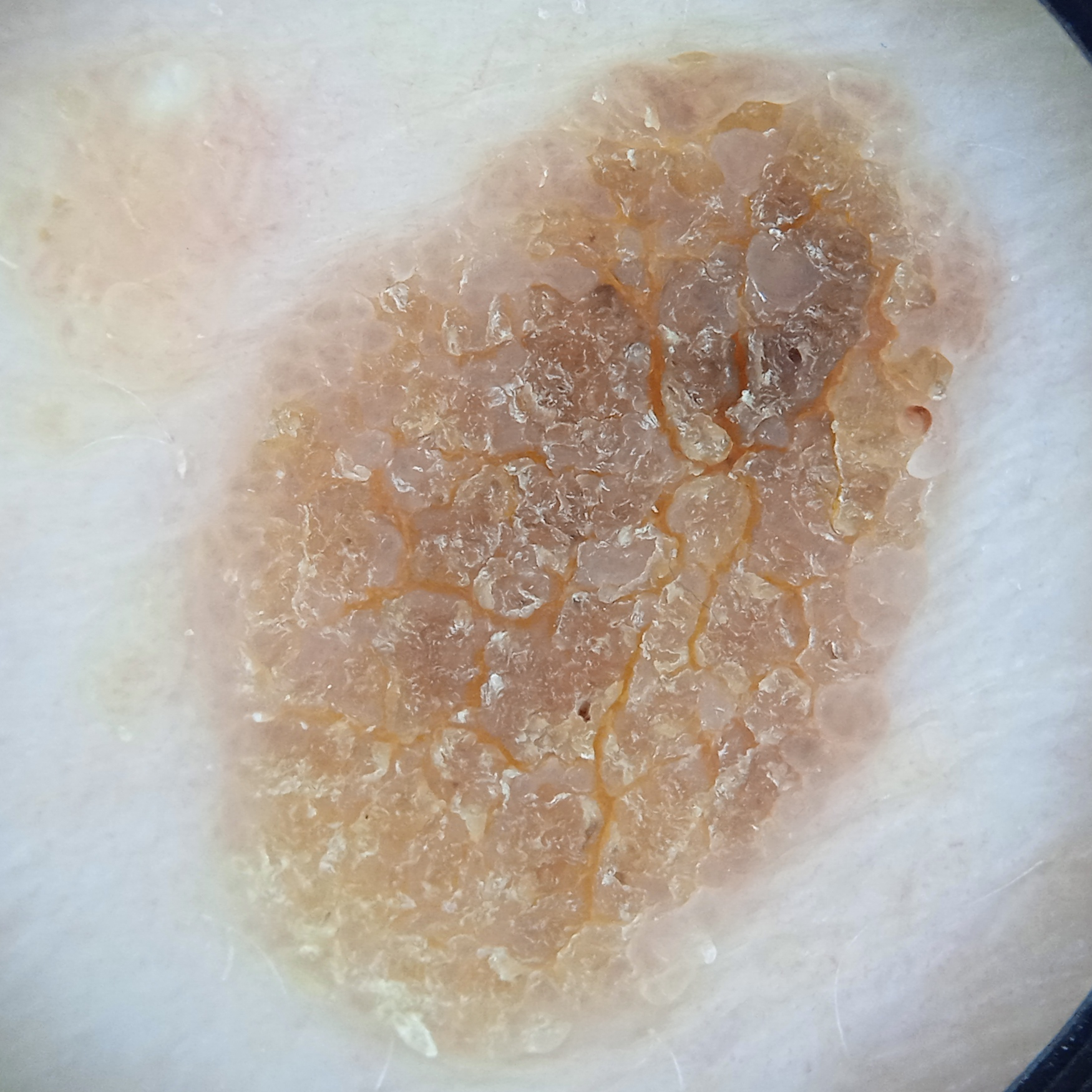Findings:
A female patient age 81. A skin lesion imaged with a dermatoscope. The lesion measures approximately 12.2 mm.
Conclusion:
The diagnostic impression was a seborrheic keratosis.